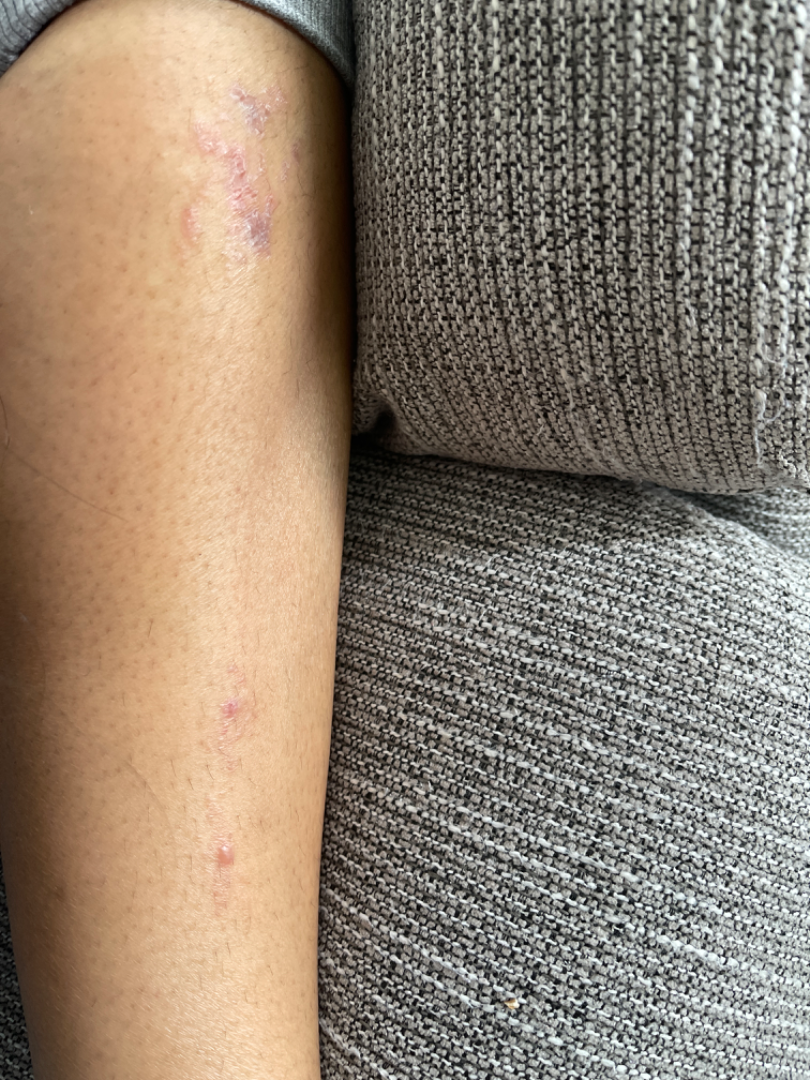Patient information:
No relevant systemic symptoms. The leg is involved. An image taken at a distance. The contributor is a female aged 30–39. The lesion is associated with itching. Present for one to four weeks. The lesion is described as rough or flaky. The patient described the issue as a rash.
Review:
On remote dermatologist review: Eczema (most likely); Tinea (remote); Cutaneous larva migrans (remote); Lichen planus/lichenoid eruption (remote); Allergic Contact Dermatitis (remote).